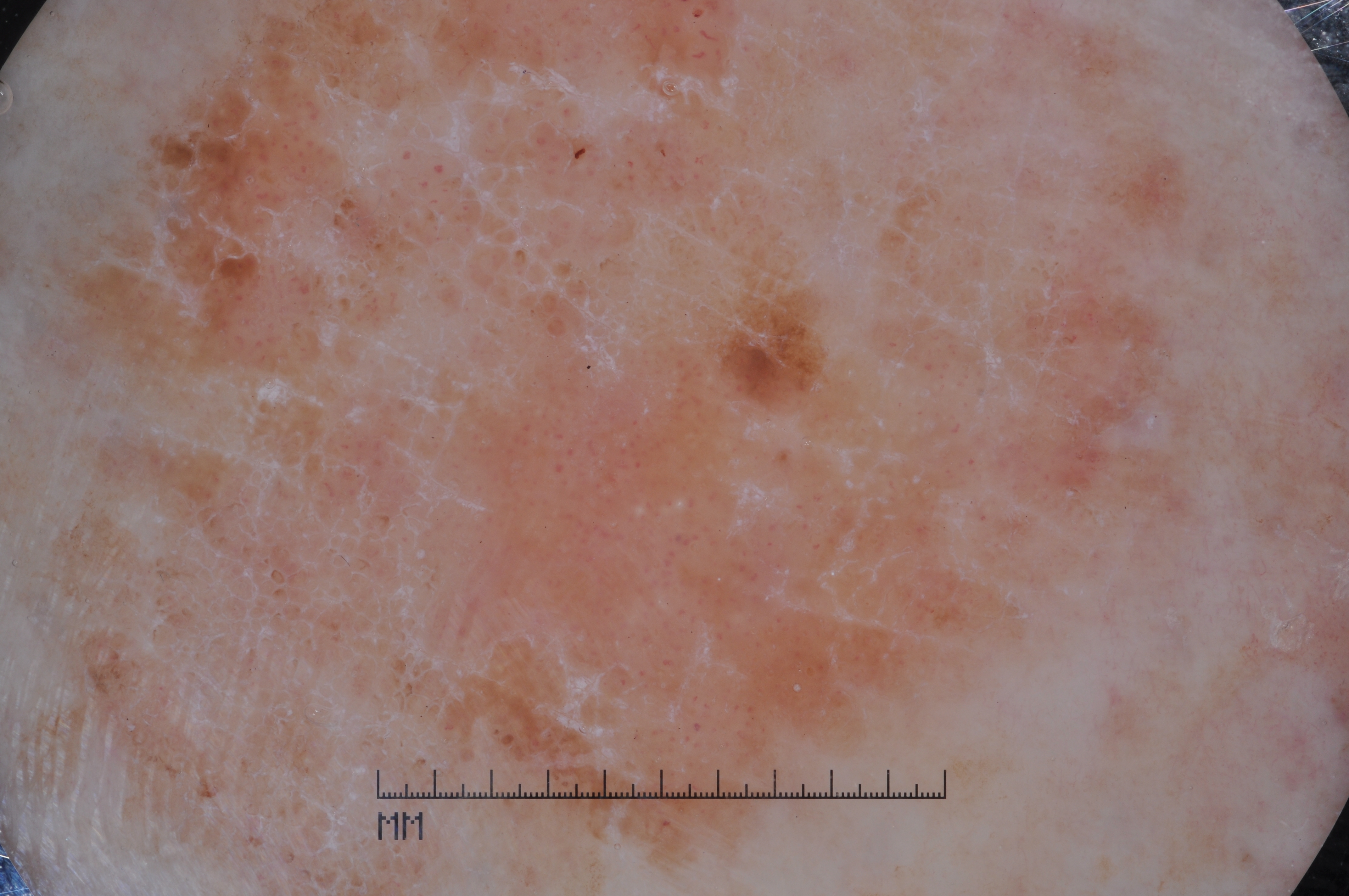patient = female, aged 68-72
image type = dermatoscopic image of a skin lesion
features = milia-like cysts; absent: pigment network, streaks, and negative network
extent = large
location = (33, 4, 1228, 895)
diagnostic label = a seborrheic keratosis